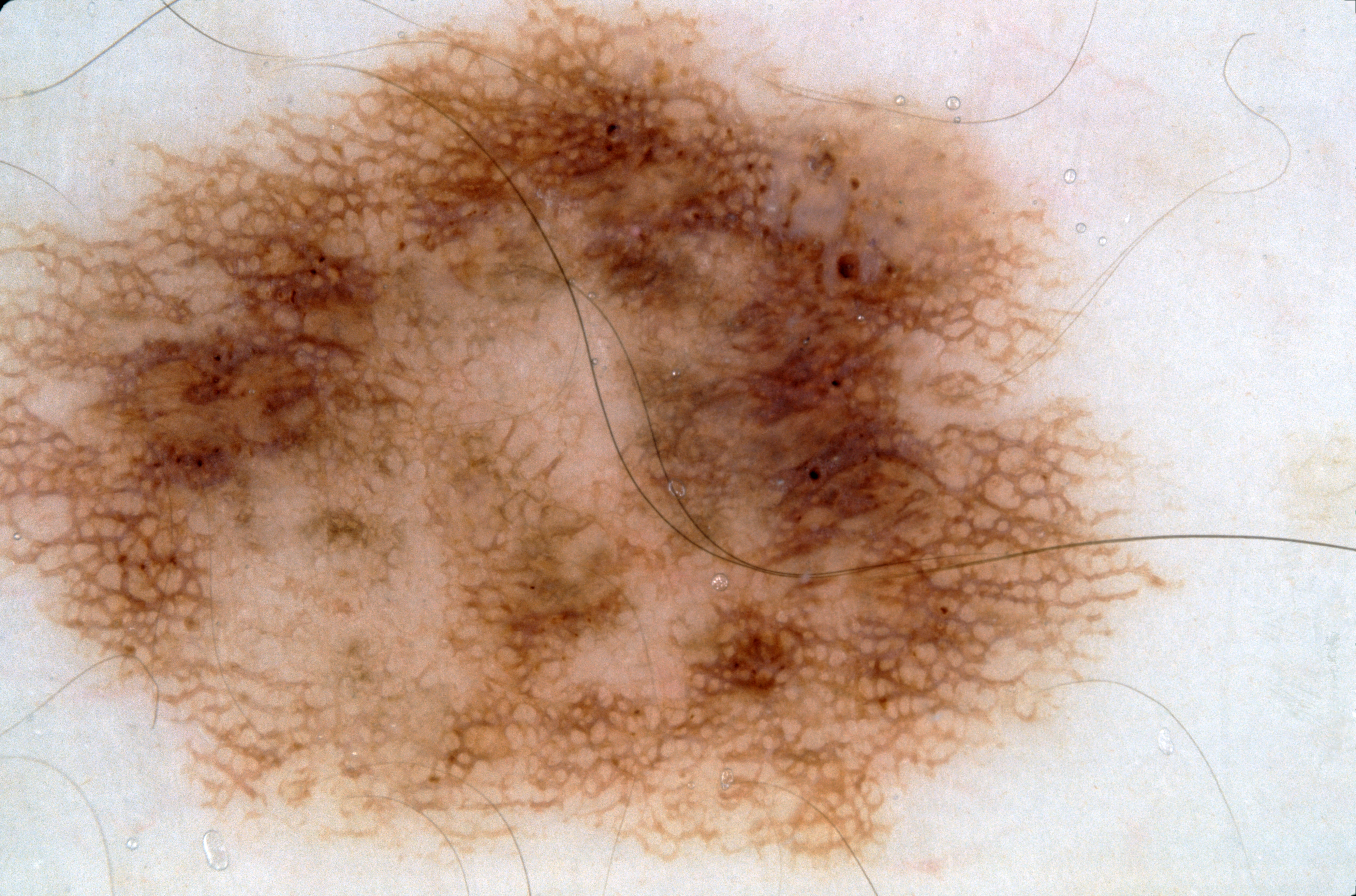A male patient, in their mid- to late 40s.
A dermoscopic close-up of a skin lesion.
The lesion extends to the edge of the dermoscopic field.
With coordinates (x1, y1, x2, y2), the lesion spans <bbox>0, 0, 1144, 875</bbox>.
Dermoscopic assessment notes pigment network.
A prominent lesion filling much of the field.
The clinical diagnosis was a melanocytic nevus.